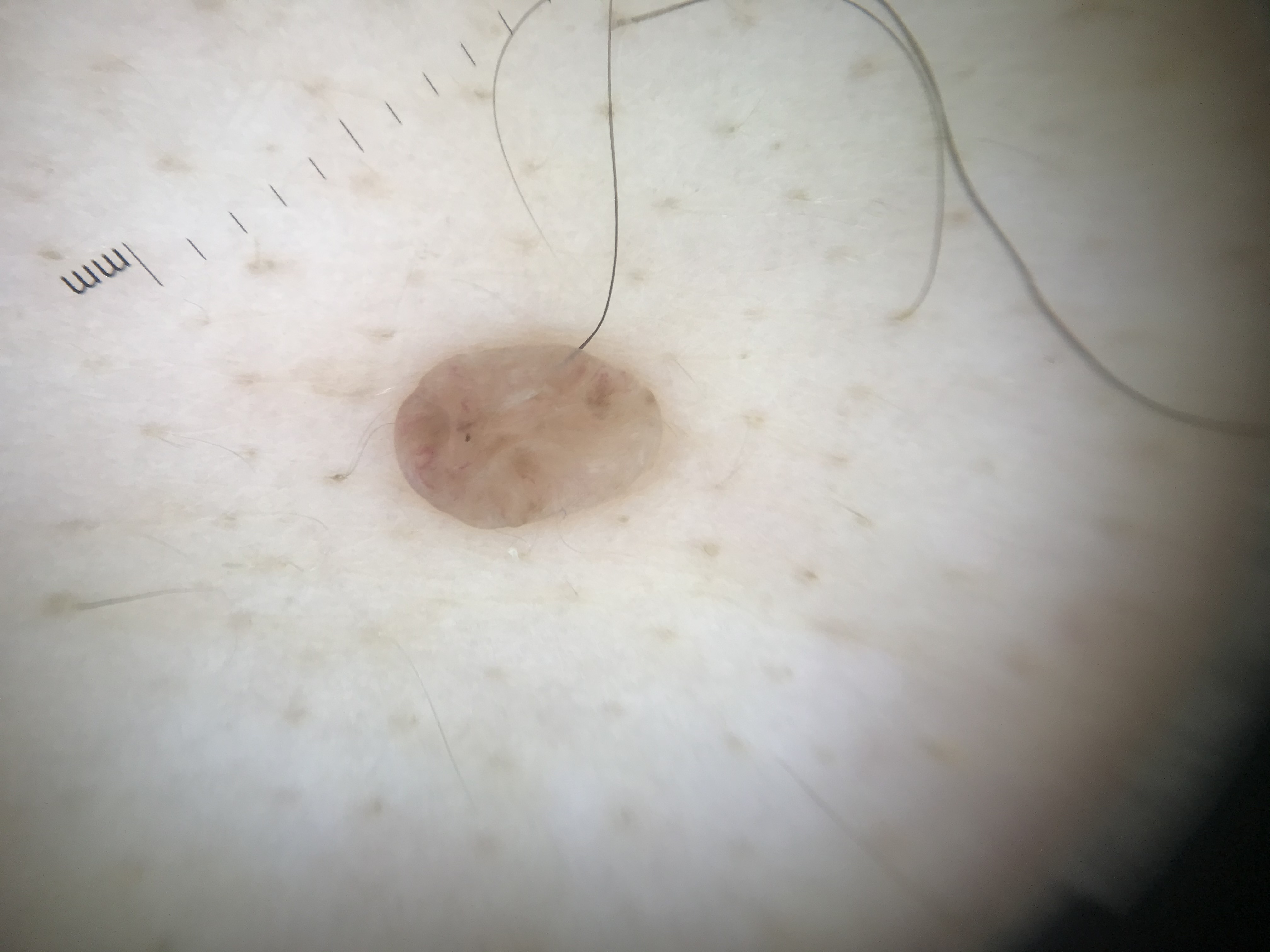image: dermoscopy
lesion_type:
  main_class: banal
  pattern: dermal
diagnosis:
  name: dermal nevus
  code: db
  malignancy: benign
  super_class: melanocytic
  confirmation: expert consensus